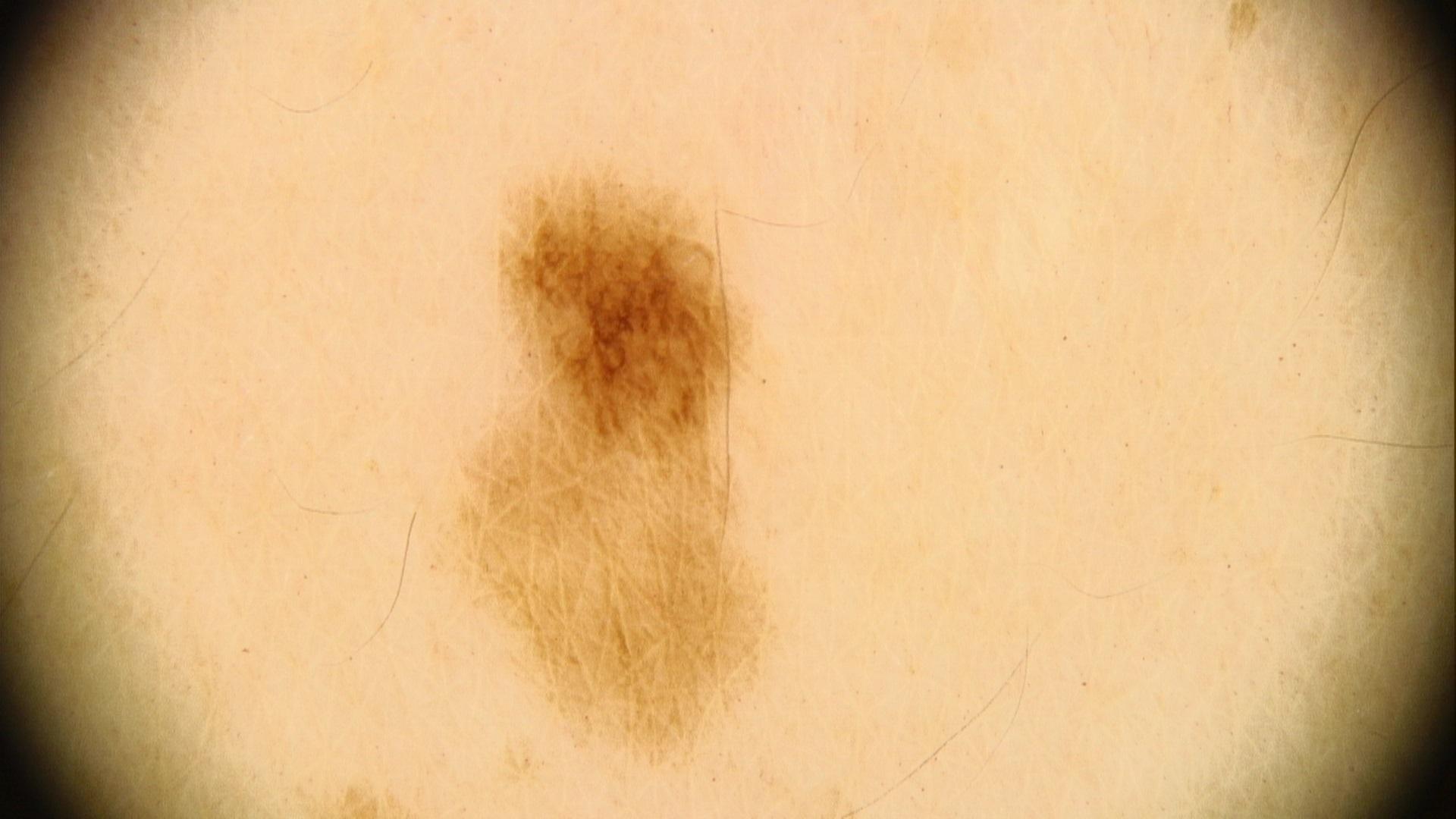A skin lesion imaged with contact-polarized dermoscopy. Recorded as FST III. The chart records melanoma in a first-degree relative but no prior melanoma. The lesion was found on the trunk. Clinically diagnosed as a nevus.